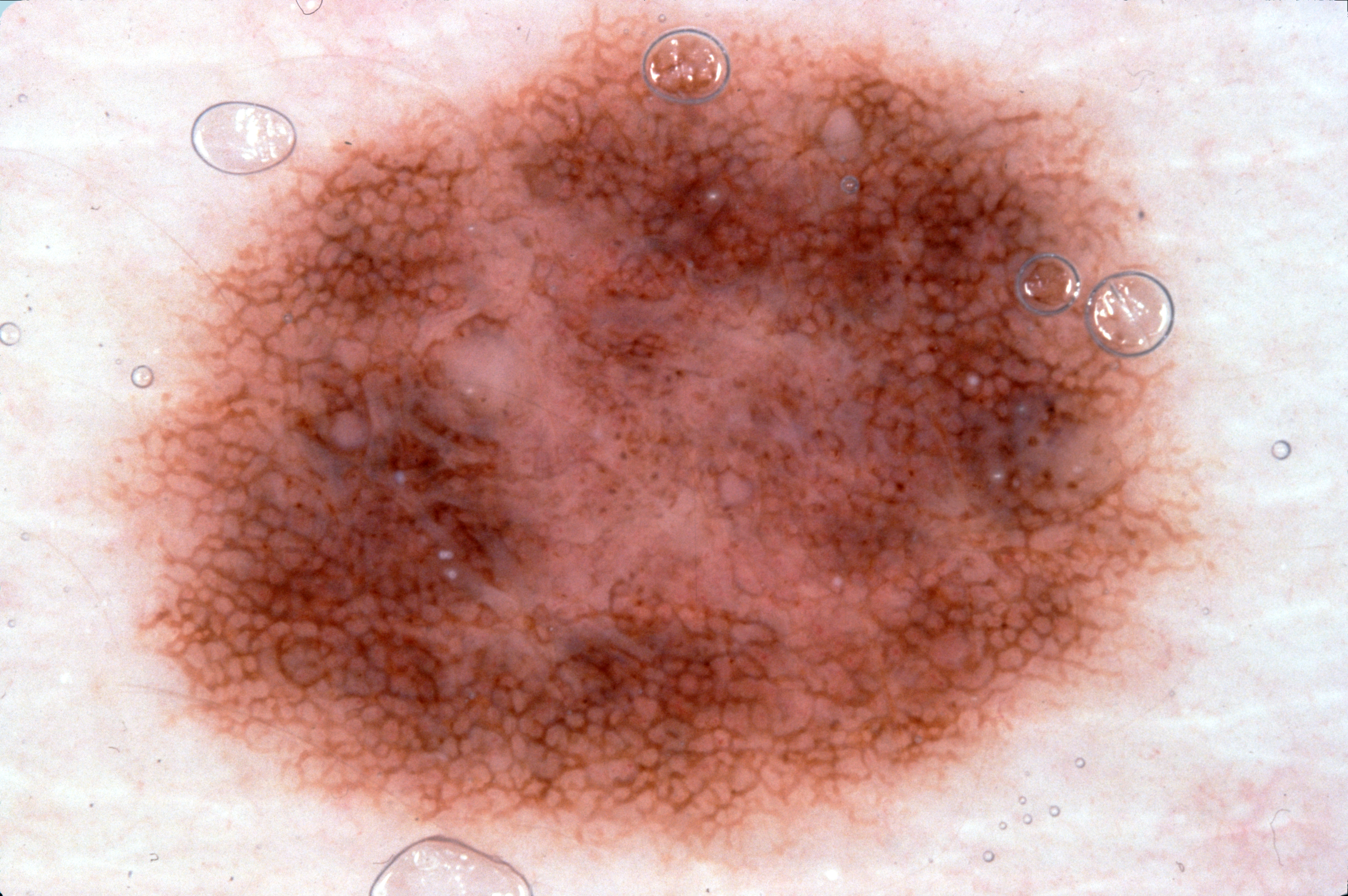Case summary: Dermoscopy of a skin lesion. On dermoscopy, the lesion shows milia-like cysts and pigment network; no streaks or negative network. The lesion spans [116, 14, 1201, 861]. A prominent lesion filling much of the field. Impression: The diagnostic assessment was a melanocytic nevus.